The patient is Fitzpatrick skin type II — 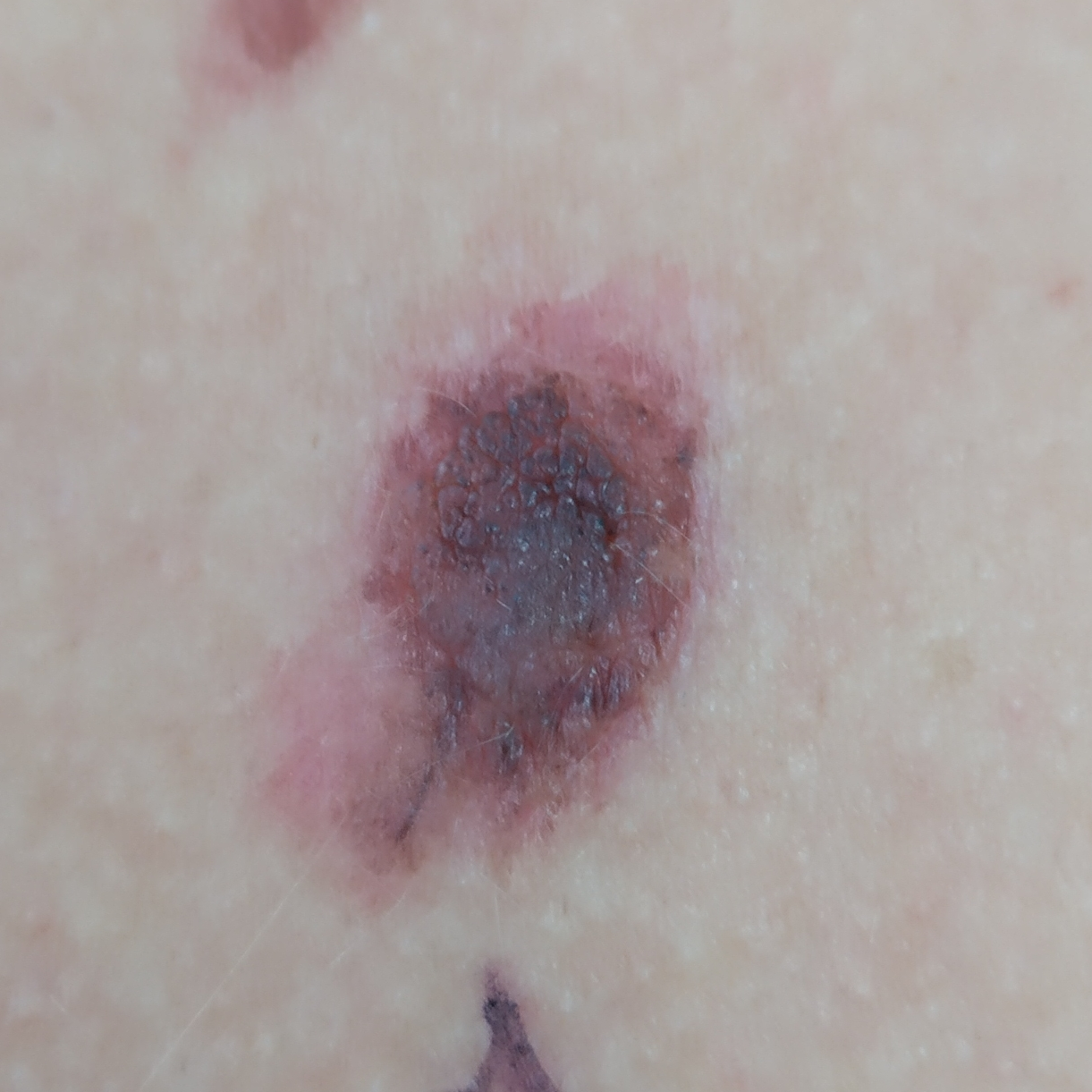The patient reports that the lesion has grown. The biopsy diagnosis was a malignancy — a melanoma.